A close-up photograph: 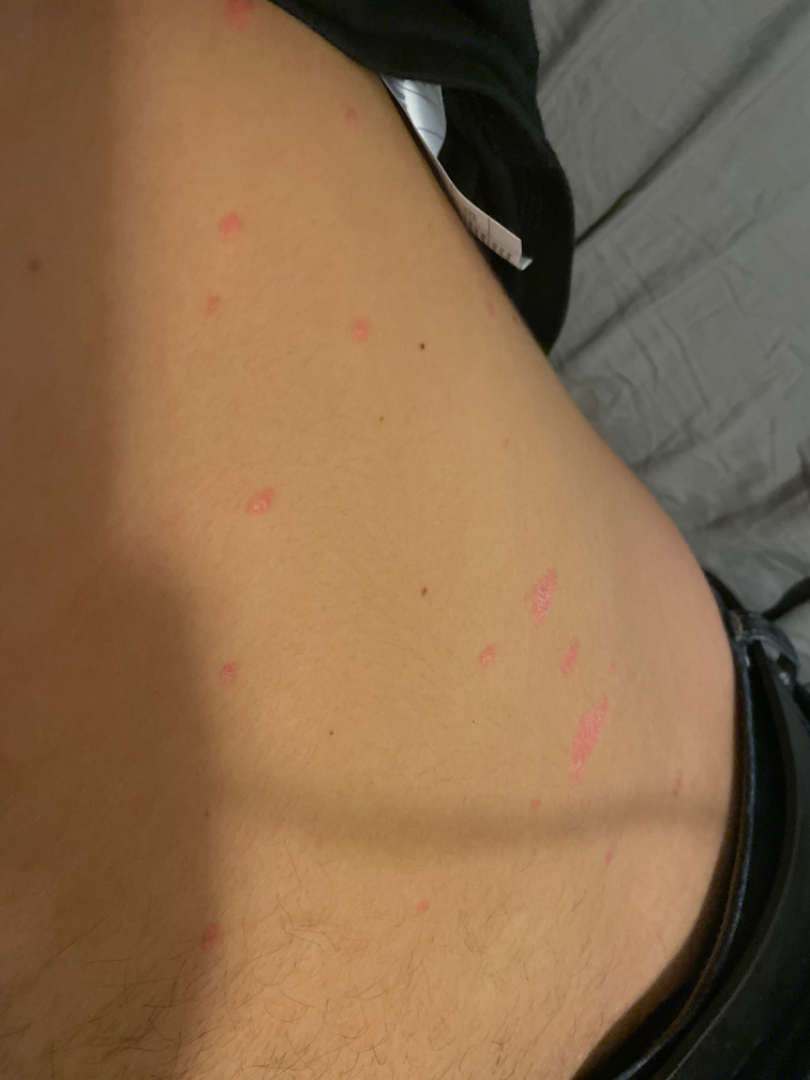Impression: On remote dermatologist review, Psoriasis (100%).